A clinical close-up of a skin lesion. Collected as part of a research study, without a referral diagnosis. The patient says their skin tans without first burning. A female patient aged 78. Numerous moles by the patient's own estimate.
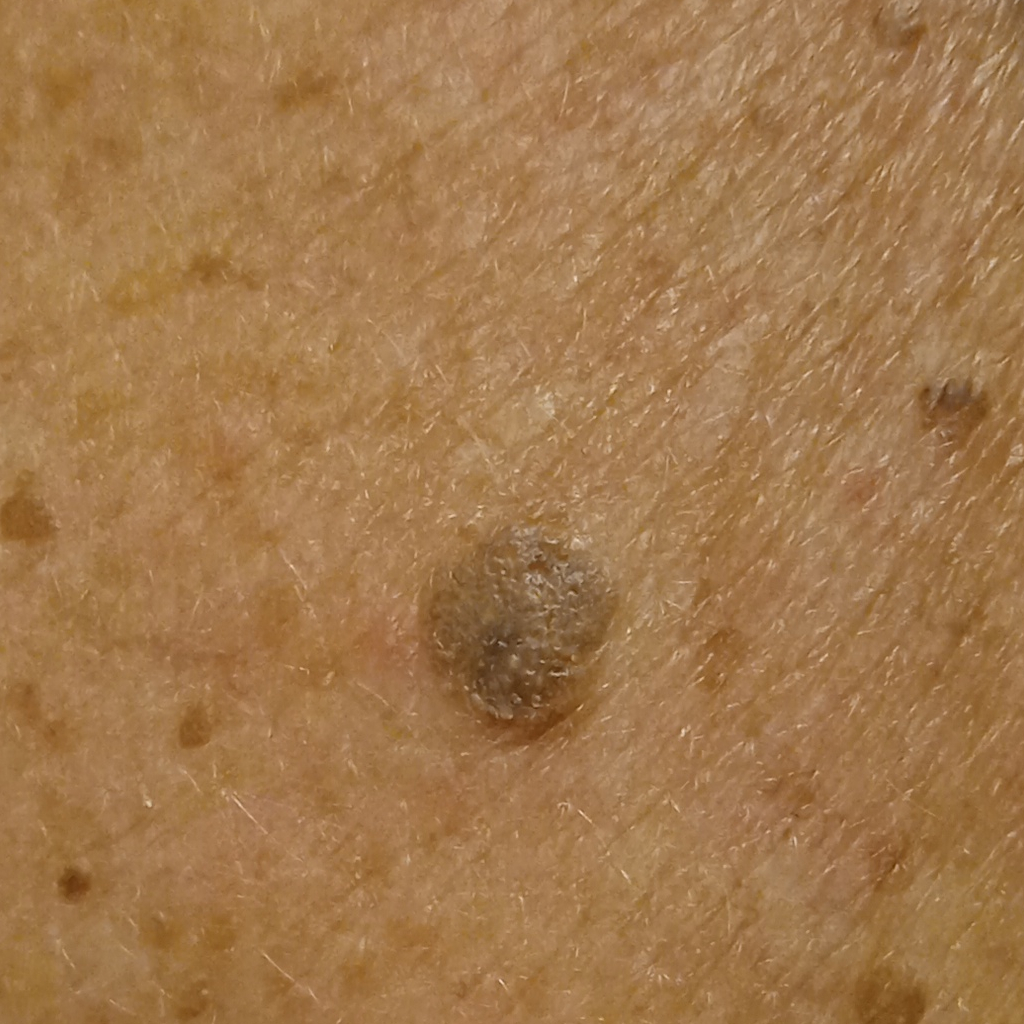Case summary:
The lesion is on the back. Measuring roughly 7.3 mm.
Impression:
The dermatologists' assessment was a seborrheic keratosis.